The patient is Fitzpatrick phototype II · a dermoscopic photograph of a skin lesion:
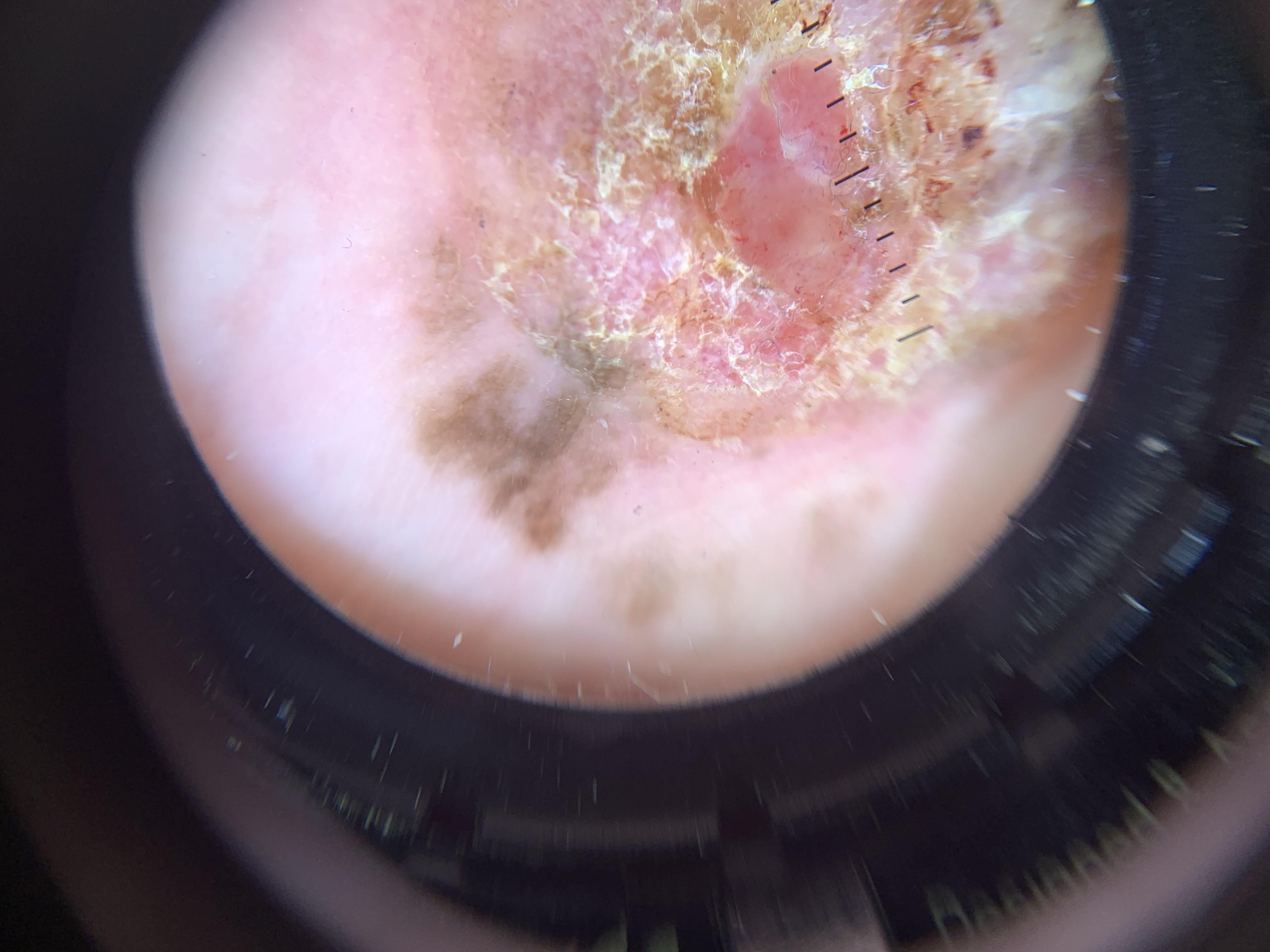Case:
• diagnosis: Melanoma (biopsy-proven)